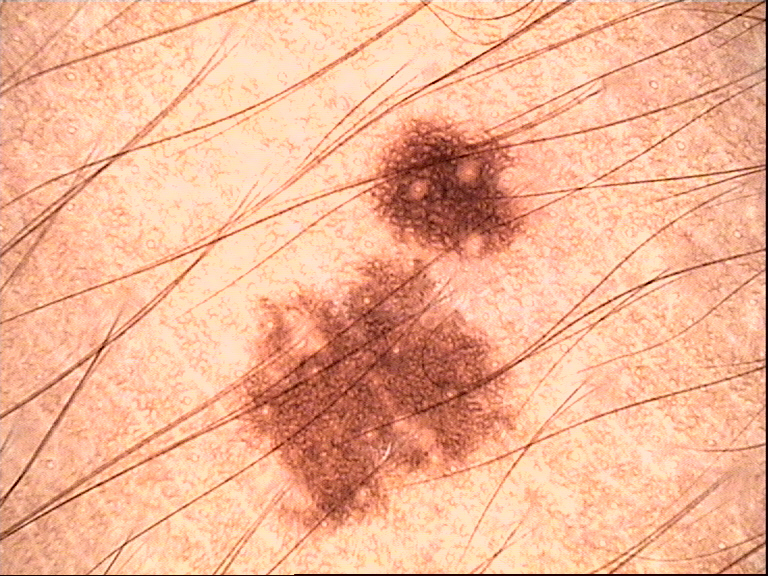The diagnostic label was a dysplastic junctional nevus.